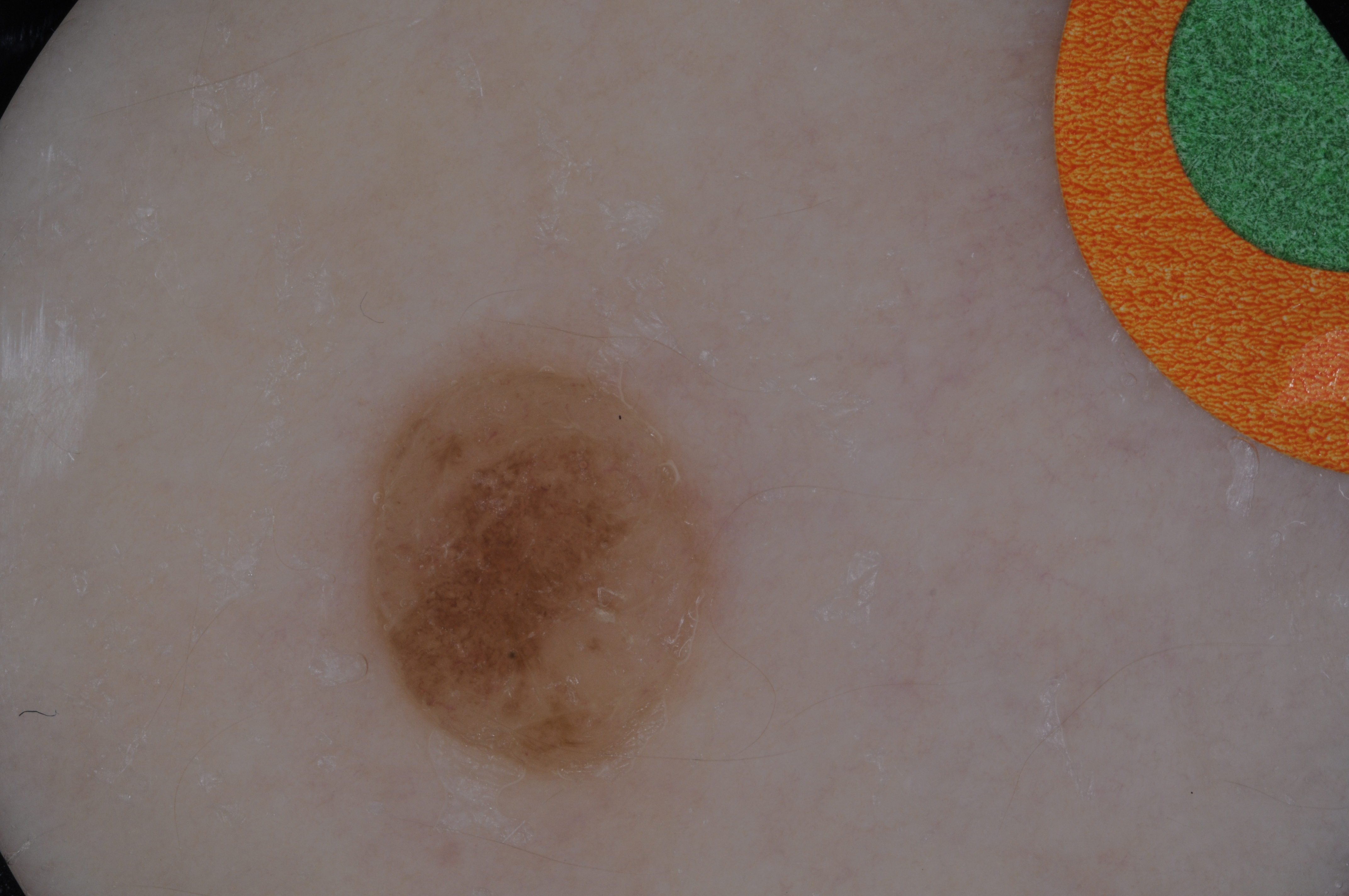  image:
    modality: dermoscopy
  lesion_location:
    bbox_xyxy:
      - 356
      - 357
      - 716
      - 786
  lesion_extent: moderate
  diagnosis:
    malignancy: benign
    provenance: clinical